The photo was captured at a distance: 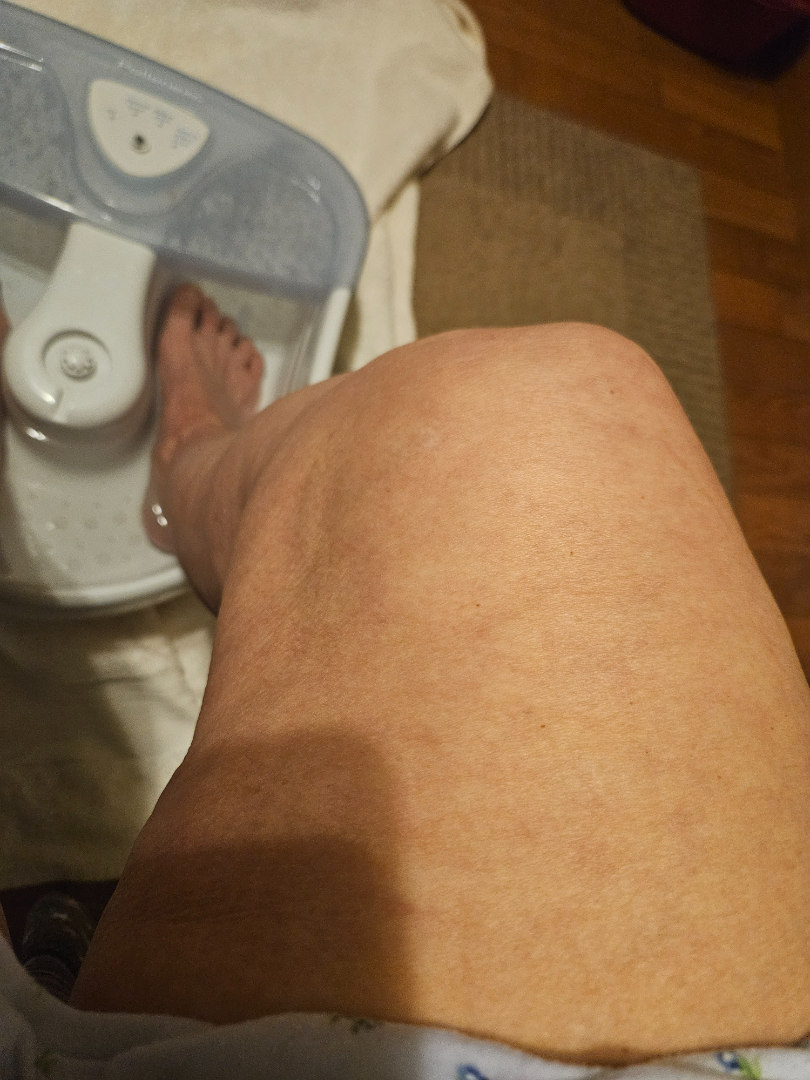Findings:
– assessment — indeterminate from the photograph